Close-up view · located on the arm:
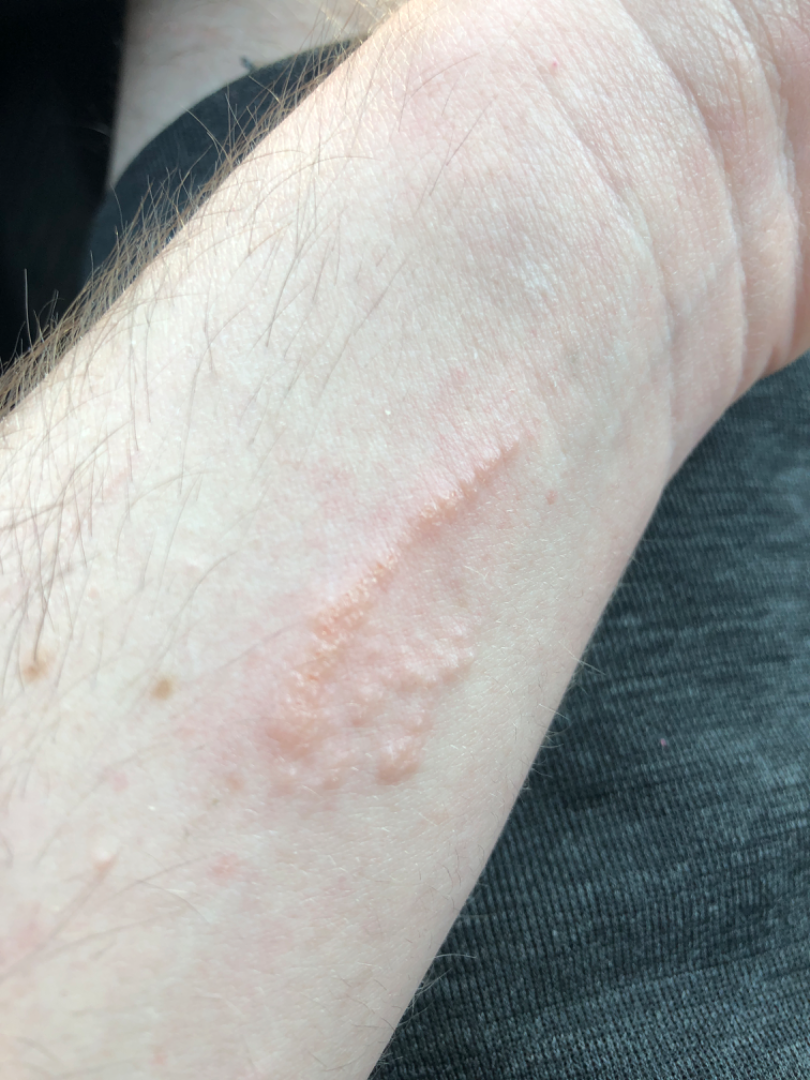Notes:
– differential diagnosis: most consistent with Allergic Contact Dermatitis